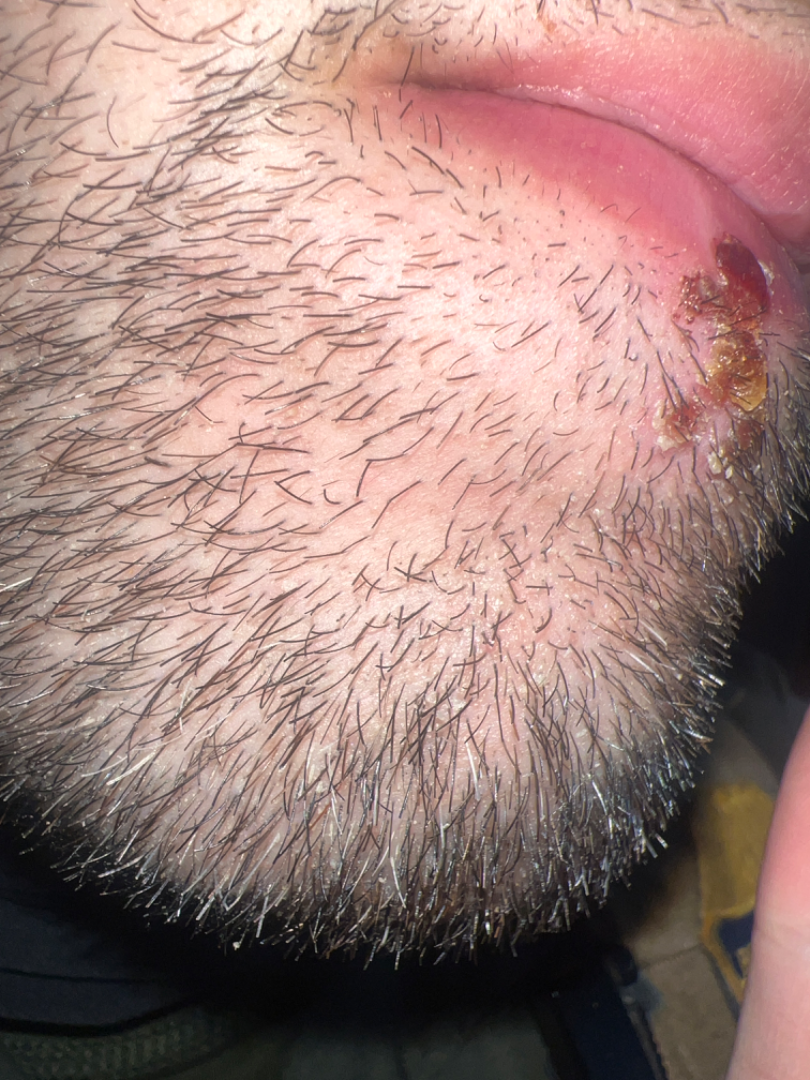The reviewing dermatologist was unable to assign a differential diagnosis from the image. The head or neck is involved. Texture is reported as fluid-filled, raised or bumpy and flat. This image was taken at an angle. Skin tone: Fitzpatrick phototype II. The patient is male.